A clinical photograph of a skin lesion. A subject aged 68 — 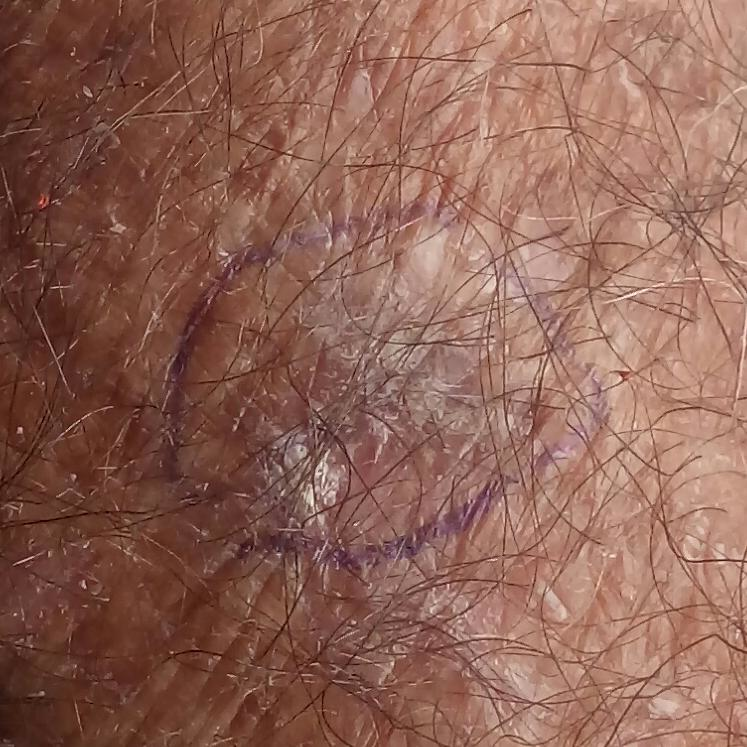- anatomic site · a forearm
- reported symptoms · itching, elevation / no growth
- impression · actinic keratosis (clinical consensus)